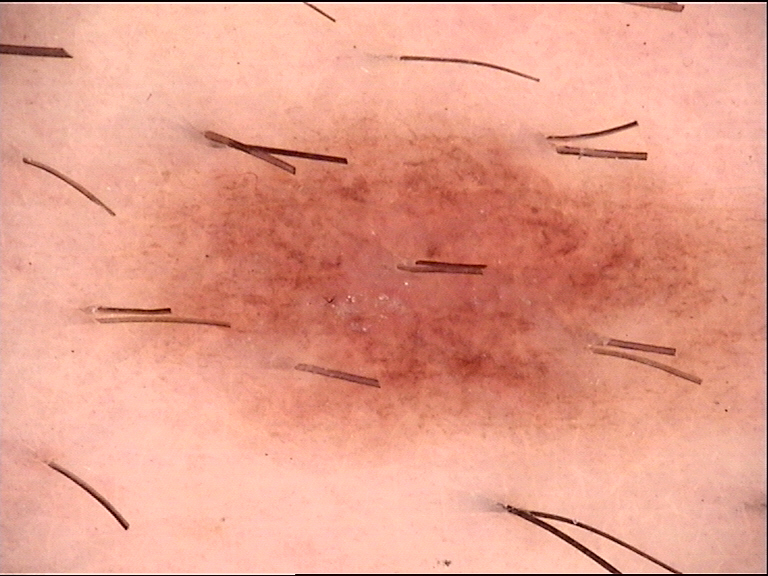{
  "image": "dermoscopy",
  "diagnosis": {
    "name": "dysplastic compound nevus",
    "code": "cd",
    "malignancy": "benign",
    "super_class": "melanocytic",
    "confirmation": "expert consensus"
  }
}